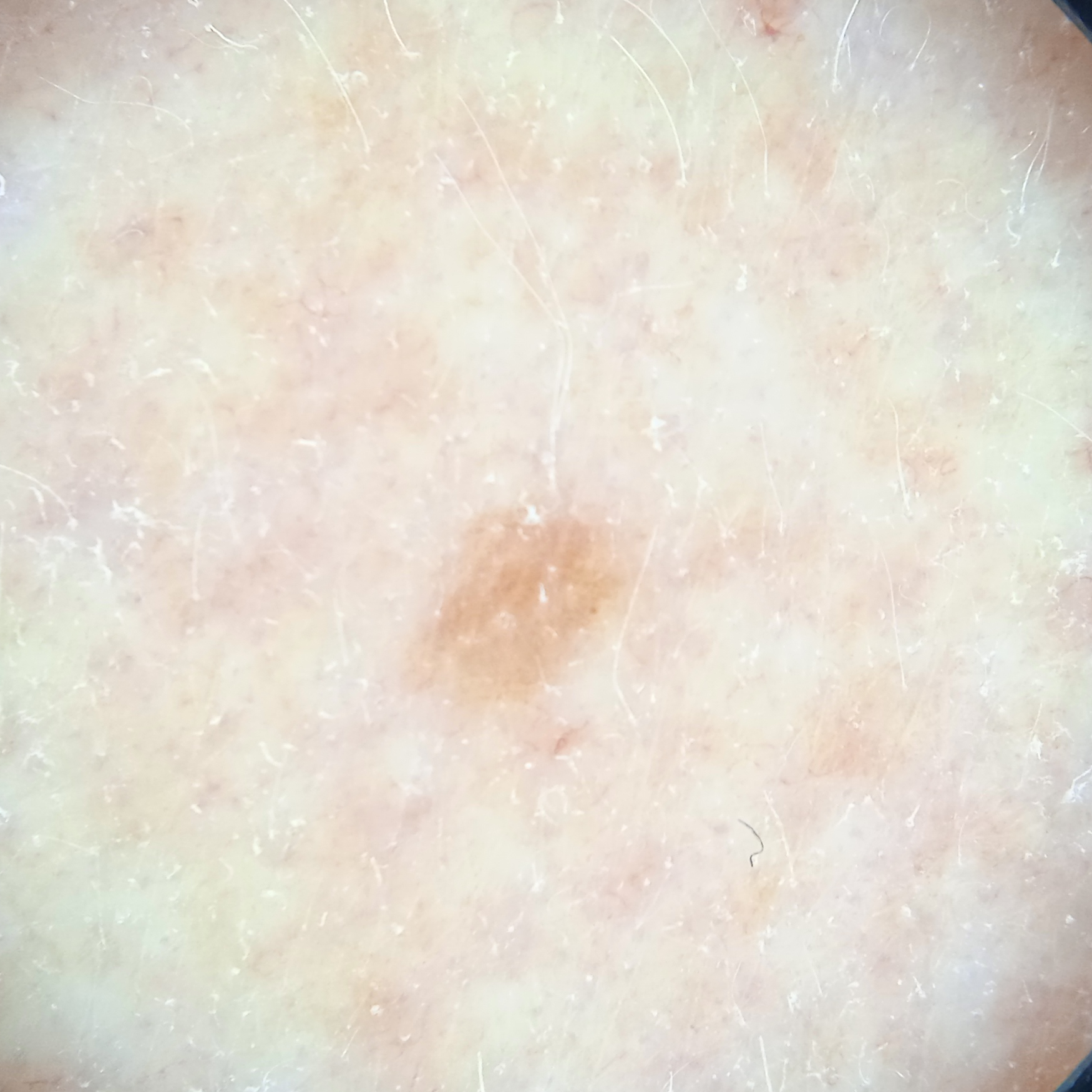The diagnostic impression was a melanocytic nevus.